The patient considered this a rash. Close-up view. The lesion is associated with bothersome appearance, enlargement and itching. The condition has been present for one to four weeks. Located on the arm: 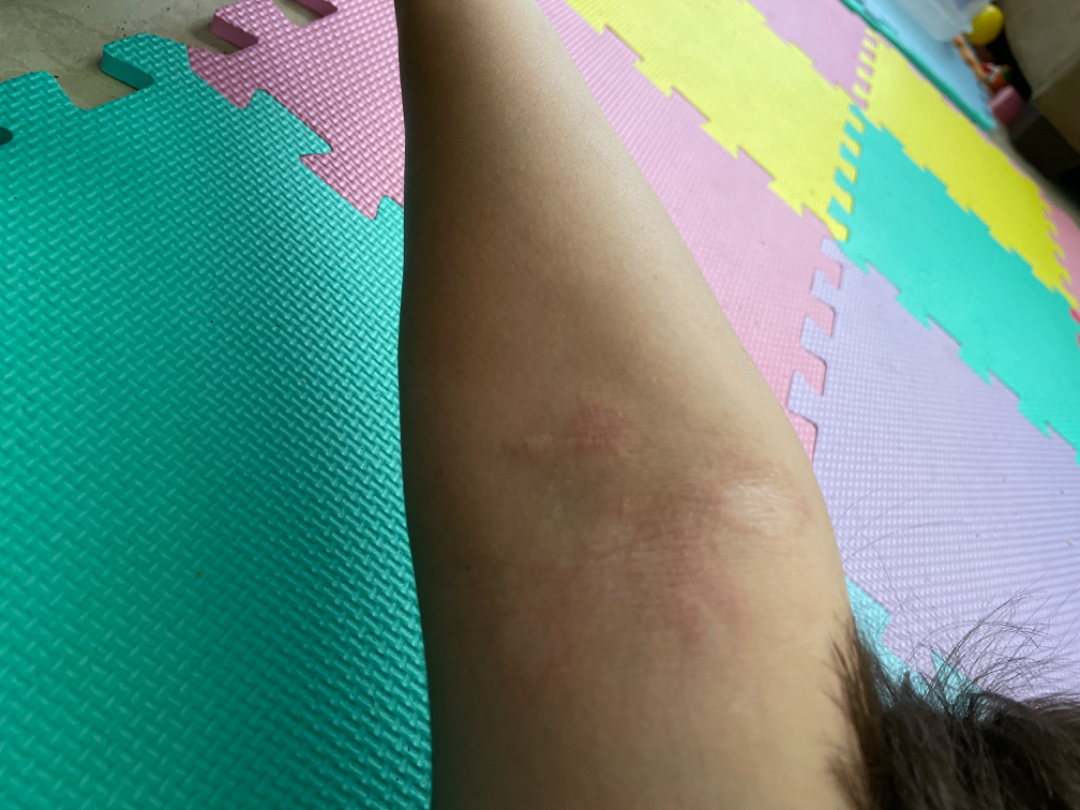On remote dermatologist review, most consistent with Eczema.